A dermoscopy image of a single skin lesion · the patient is a female in their 30s: 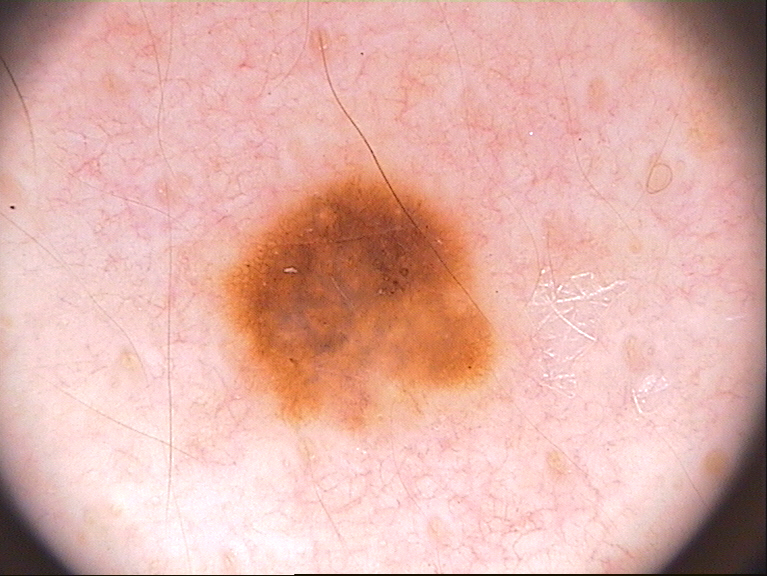Case summary:
With coordinates (x1, y1, x2, y2), the lesion occupies the region box(204, 163, 503, 446). Dermoscopy demonstrates globules and pigment network, with no streaks, negative network, or milia-like cysts.
Conclusion:
Clinically diagnosed as a melanocytic nevus.